A dermoscopic image of a skin lesion · the patient is a female aged 13 to 17:
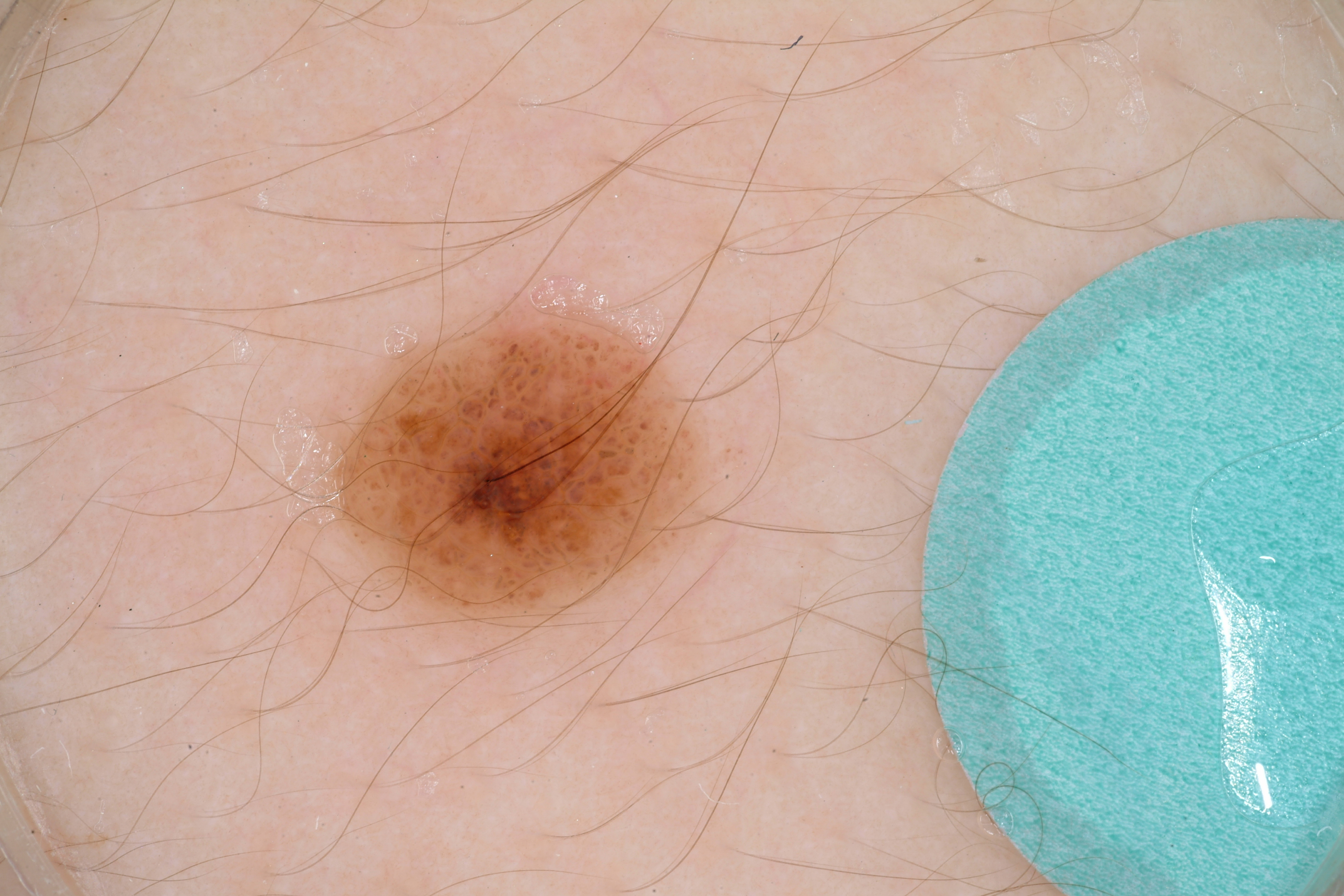| field | value |
|---|---|
| location | left=314, top=303, right=739, bottom=621 |
| dermoscopic features not present | streaks, negative network, milia-like cysts, and pigment network |
| extent | moderate |
| assessment | a melanocytic nevus |